History notes alcohol use, prior malignancy (patient or family), no prior skin cancer (patient or family), and no pesticide exposure · a clinical close-up photograph of a skin lesion.
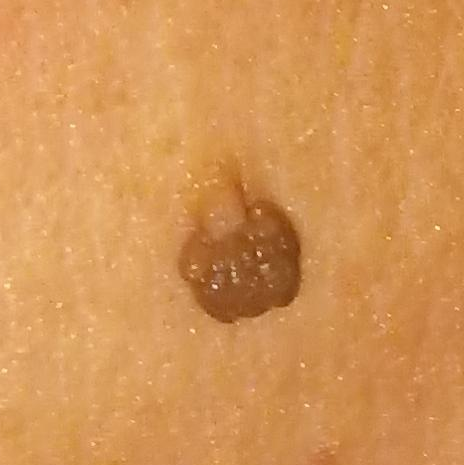Clinical context: The lesion measures approximately 20 × 20 mm. Per patient report, the lesion has grown and is elevated. Impression: Consistent with a nevus.